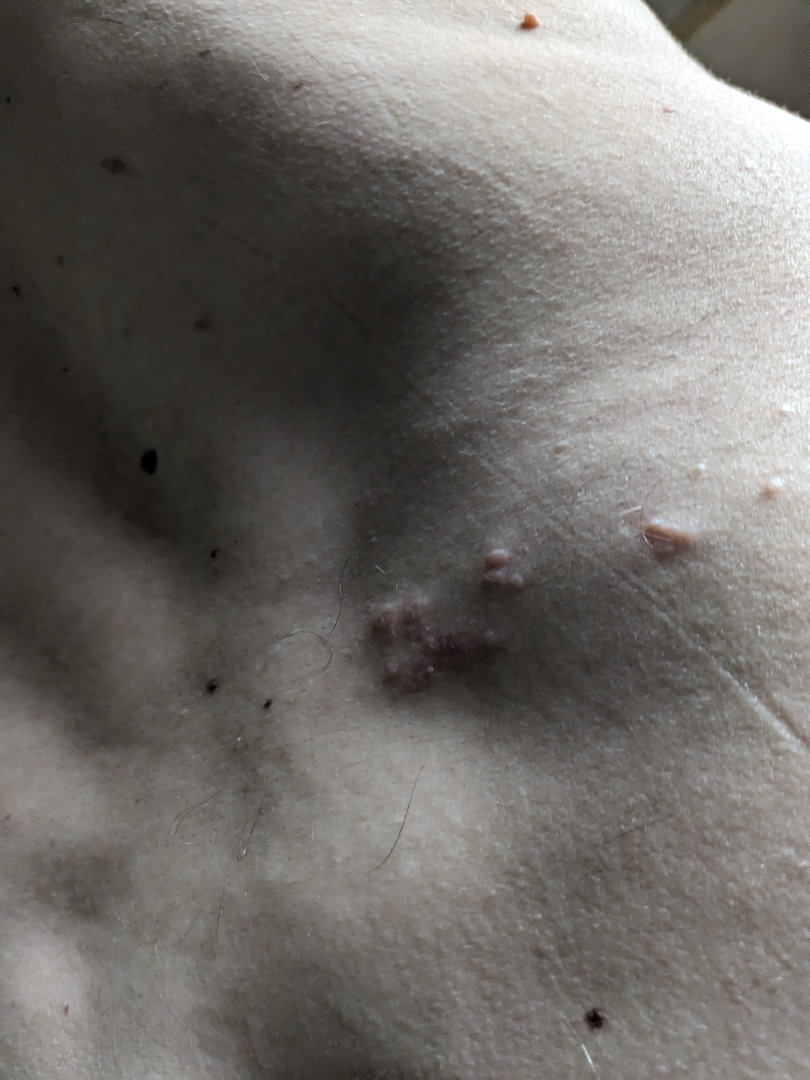Review: No differential diagnosis could be assigned on photographic review.